The patient is female, the lesion involves the arm and leg, the photograph is a close-up of the affected area: 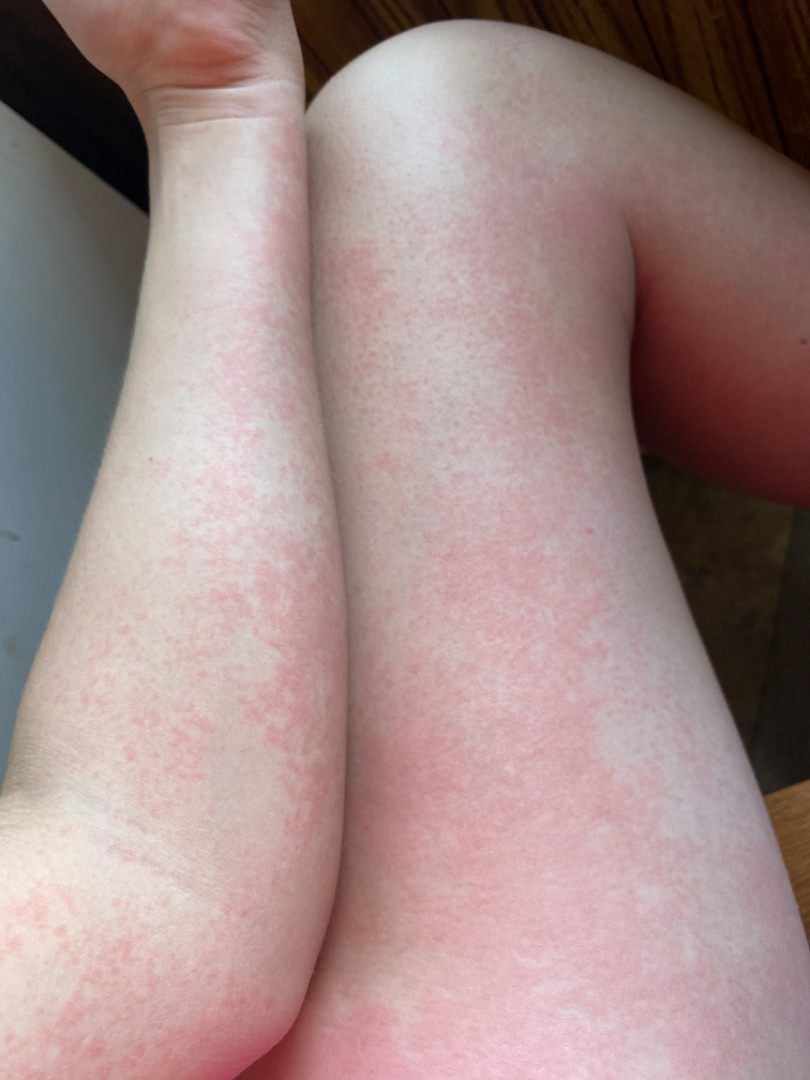reported symptoms — burning and itching
impression — Viral Exanthem (primary); Drug Rash (possible); Hypersensitivity (unlikely)